The subject is a male aged approximately 65, a dermatoscopic image of a skin lesion:
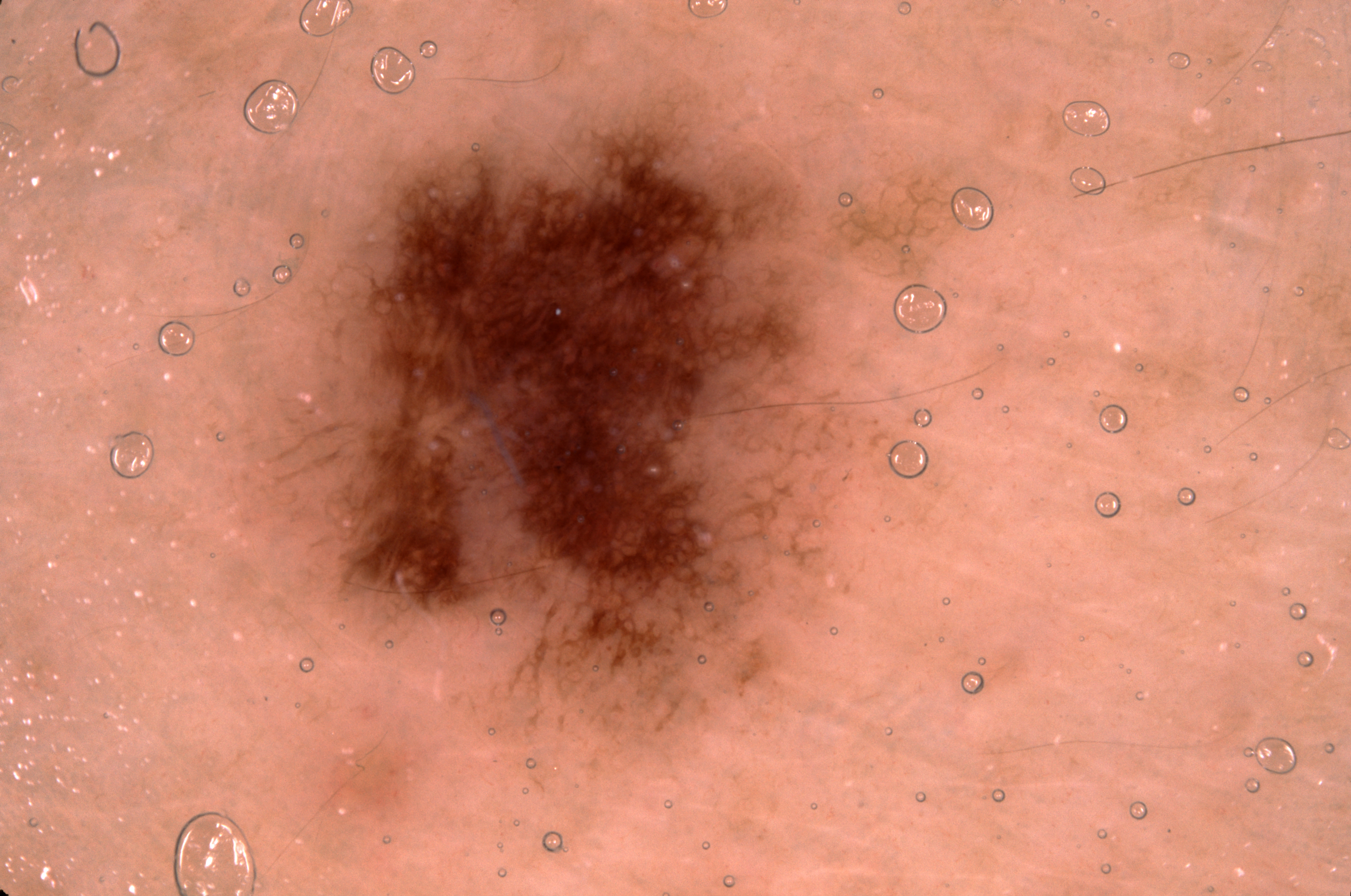Q: What is the lesion's bounding box?
A: 236, 68, 987, 746
Q: What dermoscopic features are present?
A: pigment network and milia-like cysts
Q: What is the diagnosis?
A: a melanocytic nevus